The patient notes itching; female subject, age 18–29; this is a close-up image; the patient notes the lesion is raised or bumpy and rough or flaky; the patient notes the condition has been present for one to four weeks; located on the leg:
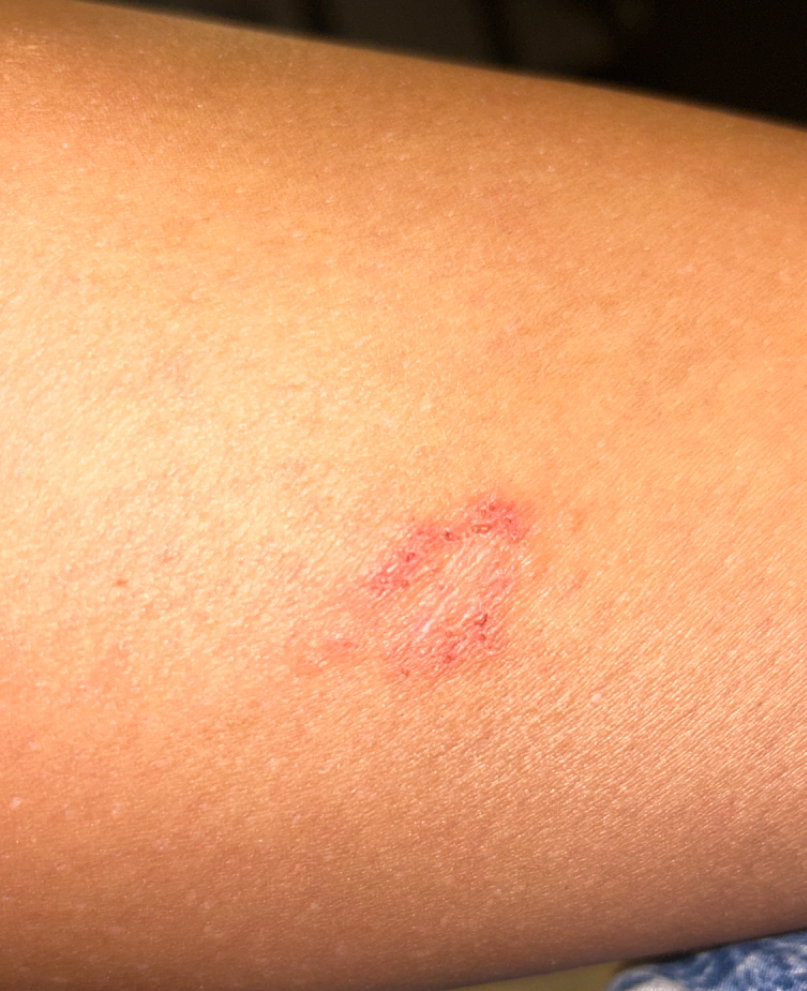{"differential": {"leading": ["Superficial wound of body region"], "considered": ["Tinea", "Eczema"]}}